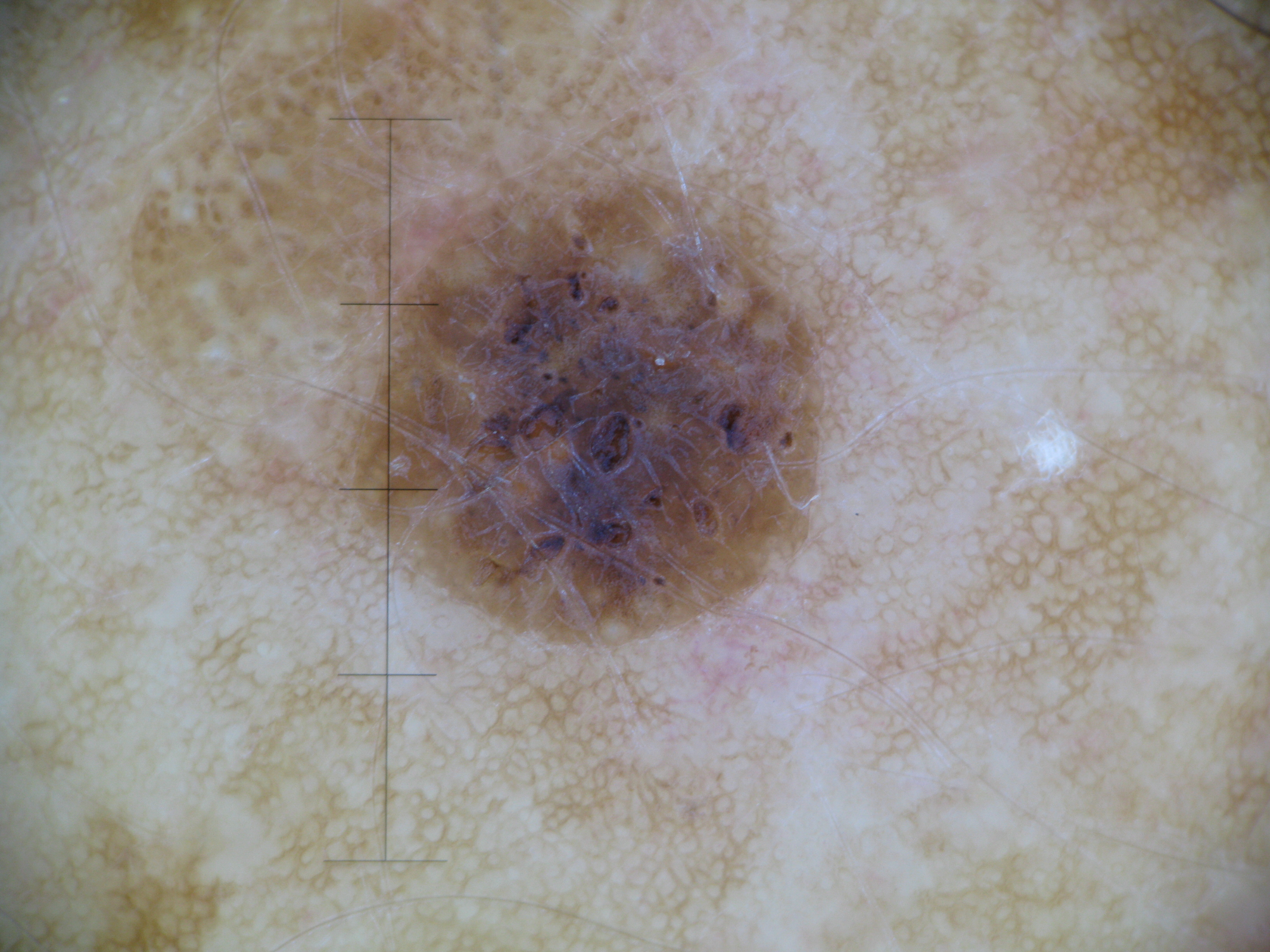diagnosis: seborrheic keratosis (expert consensus).